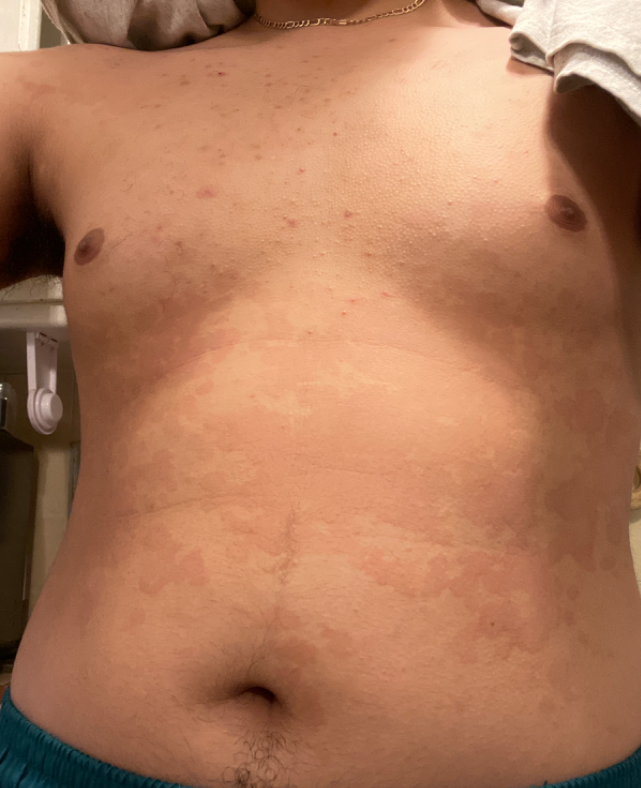  texture: flat
  duration: one to three months
  patient: male, age 18–29
  symptoms: none reported
  shot_type: at a distance
  body_site:
    - back of the torso
    - front of the torso
  differential:
    leading:
      - Tinea Versicolor
    considered:
      - Urticaria
    unlikely:
      - Pityriasis rubra pilaris
      - Psoriasis